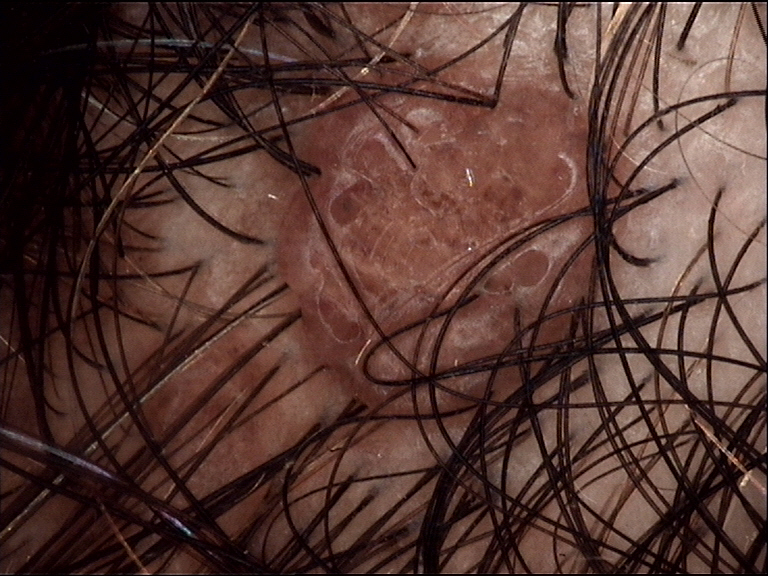image type = dermoscopy
diagnostic label = dermal nevus (expert consensus)